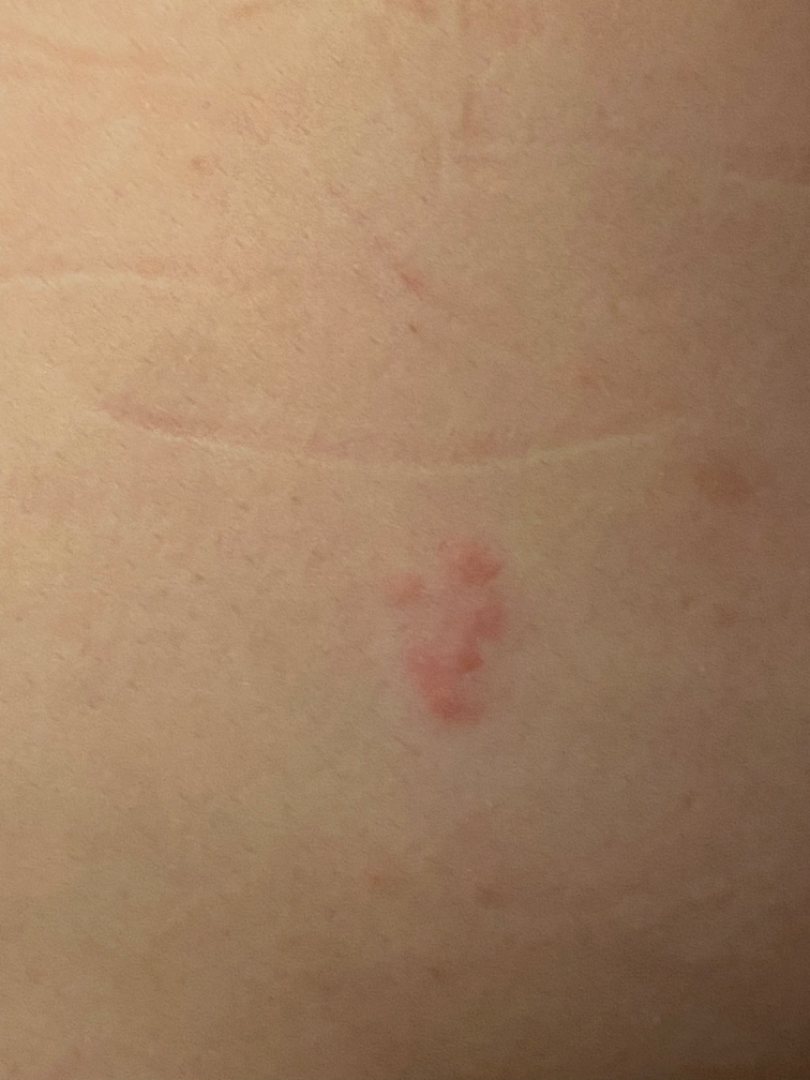Q: Could the case be diagnosed?
A: ungradable on photographic review
Q: Texture?
A: raised or bumpy
Q: What is the affected area?
A: back of the torso
Q: Constitutional symptoms?
A: none reported
Q: What symptoms does the patient report?
A: itching
Q: Who is the patient?
A: female, age 18–29
Q: Image view?
A: close-up
Q: How long has this been present?
A: about one day
Q: How does the patient describe it?
A: a rash